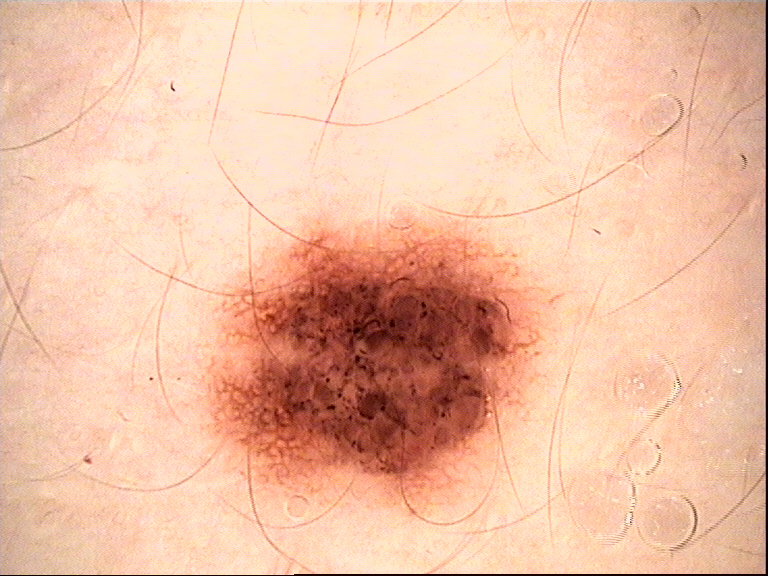A dermoscopic photograph of a skin lesion. Labeled as a dysplastic compound nevus.